A dermoscopic photograph of a skin lesion.
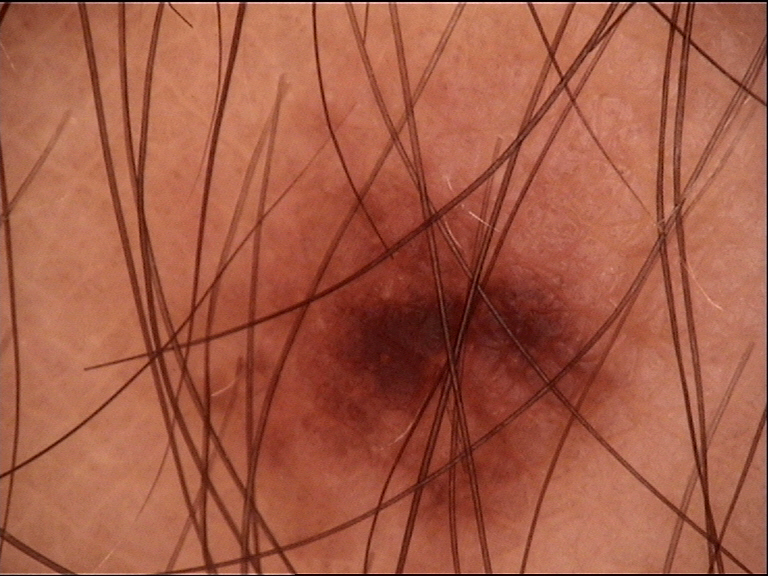{
  "lesion_type": {
    "main_class": "banal",
    "pattern": "junctional"
  },
  "diagnosis": {
    "name": "junctional nevus",
    "code": "jb",
    "malignancy": "benign",
    "super_class": "melanocytic",
    "confirmation": "expert consensus"
  }
}